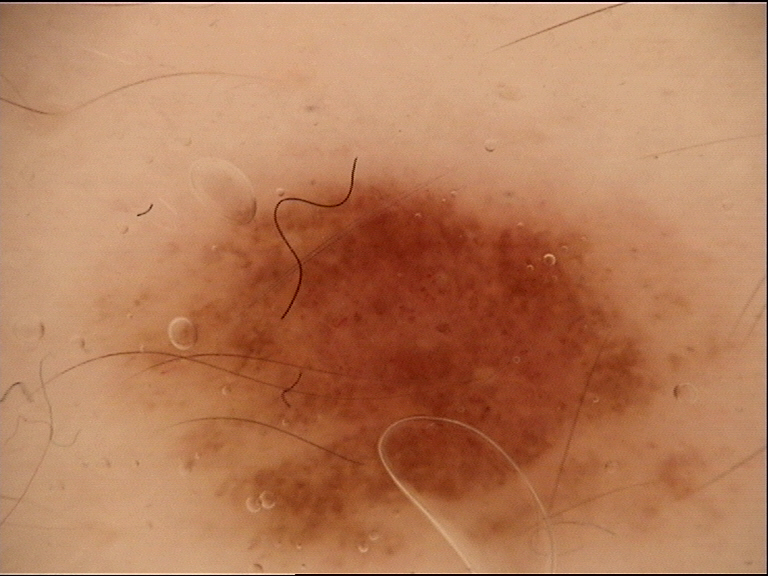Classified as a dysplastic junctional nevus.